This is a close-up image · the patient did not report lesion symptoms · the condition has been present for less than one week · located on the arm — 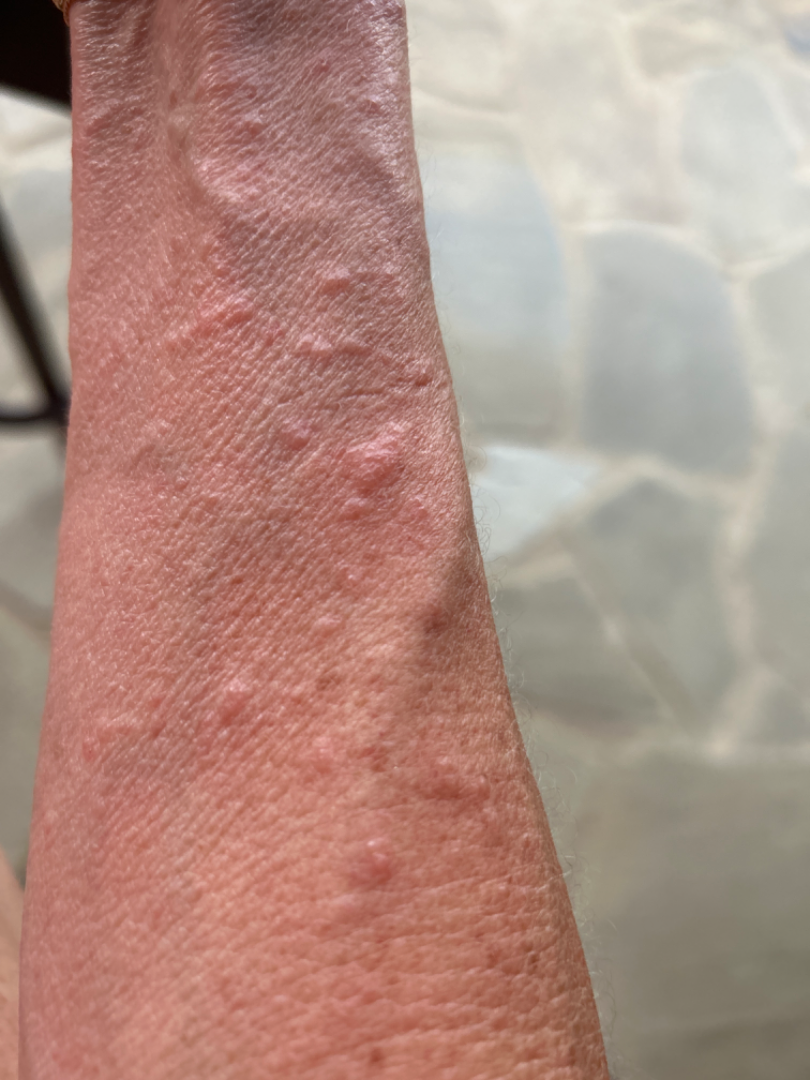{"differential": {"leading": ["Allergic Contact Dermatitis"], "considered": ["Herpes Zoster"]}}